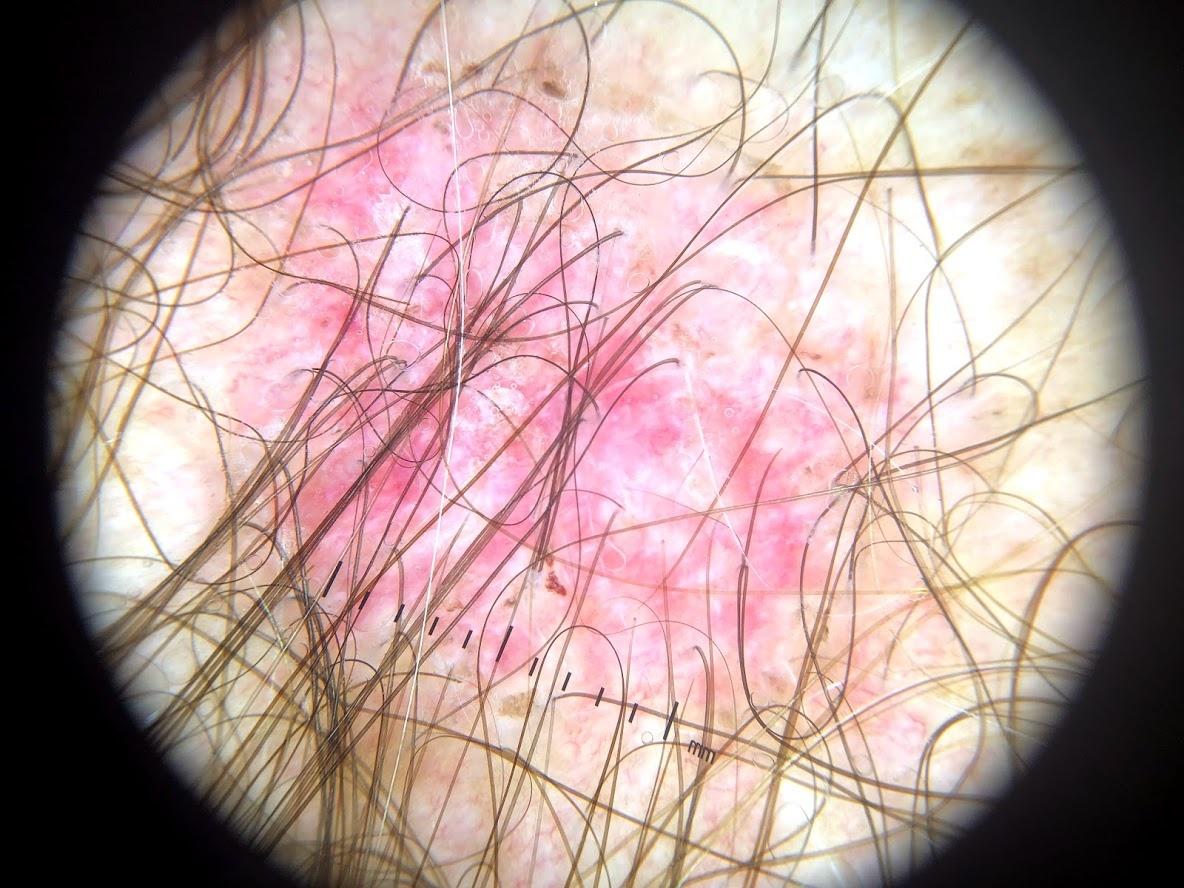Dermoscopy of a skin lesion. The patient was assessed as Fitzpatrick skin type III. Histopathological examination showed a malignant, adnexal lesion — a basal cell carcinoma.